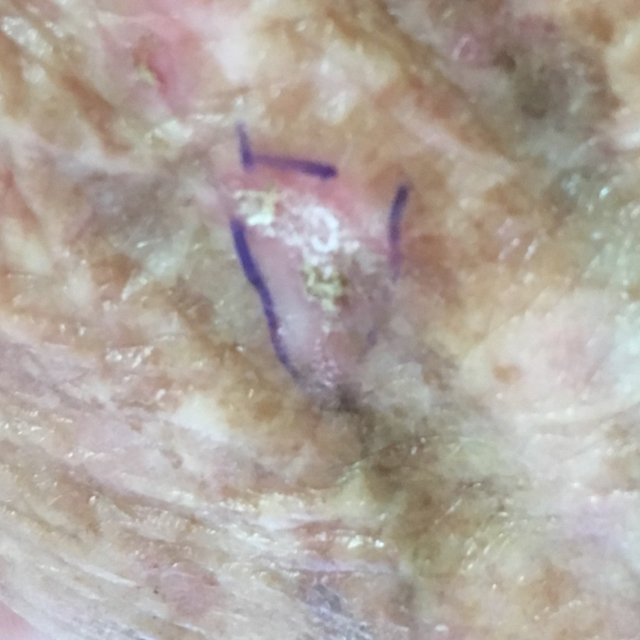A clinical photograph of a skin lesion.
A patient aged 75.
The lesion is located on a hand.
The patient reports that the lesion itches and is elevated, but has not grown.
Expert review favored an actinic keratosis.